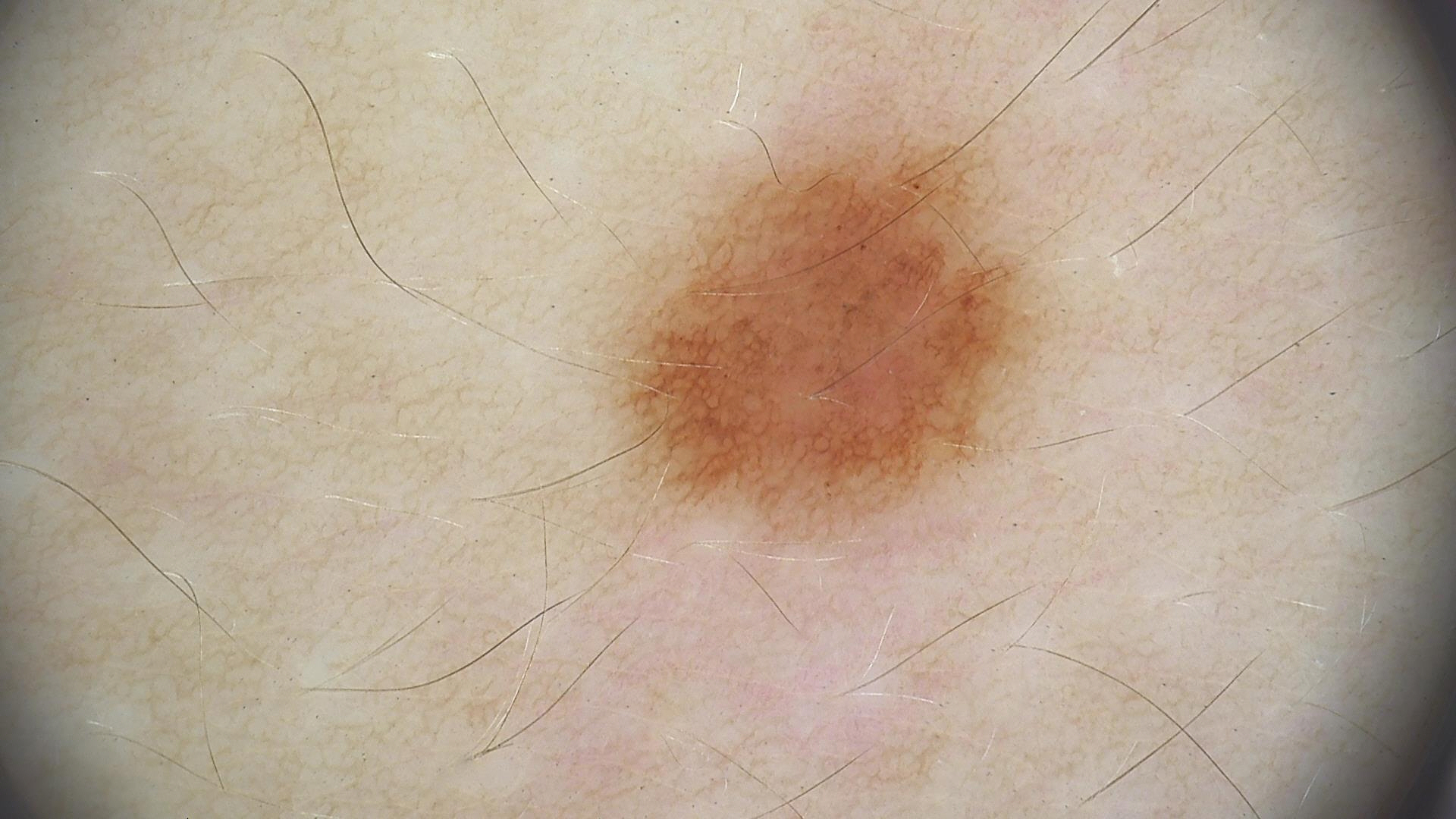{"image": "dermoscopy", "diagnosis": {"name": "dysplastic junctional nevus", "code": "jd", "malignancy": "benign", "super_class": "melanocytic", "confirmation": "expert consensus"}}